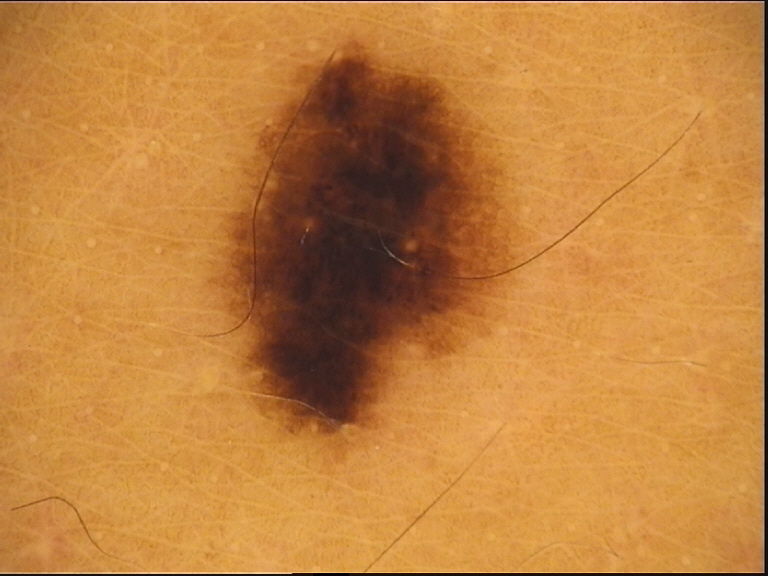A dermoscopic close-up of a skin lesion. Labeled as a benign lesion — a dysplastic junctional nevus.